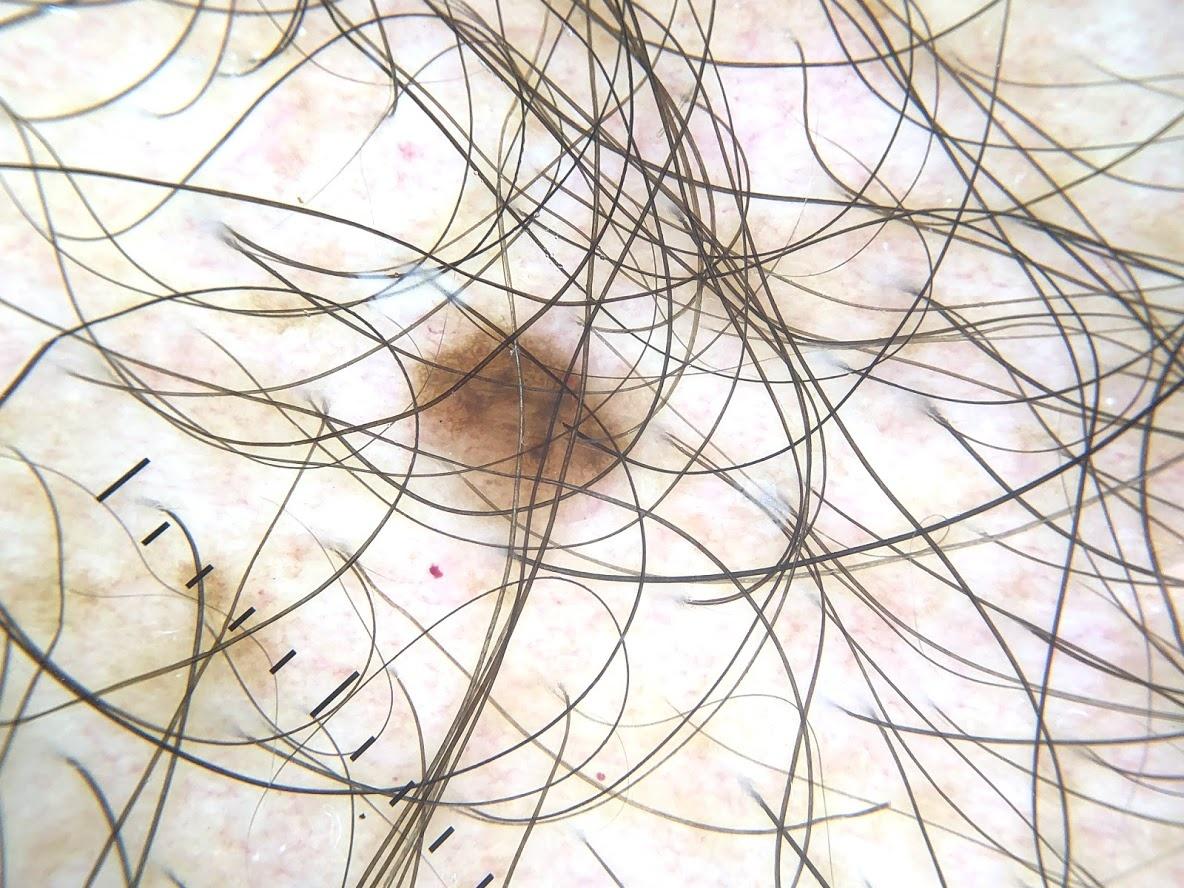image = contact-polarized dermoscopy
skin type = II
subject = male, approximately 55 years of age
melanoma history = no melanoma in first-degree relatives and no previous melanoma
pathology = Nevus (biopsy-proven)